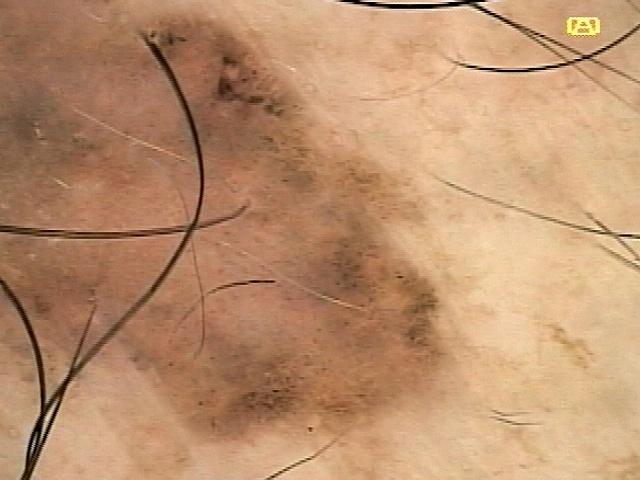image: contact-polarized dermoscopy
FST: II
patient: male, aged around 70
diagnostic label: Squamous cell carcinoma (biopsy-proven)